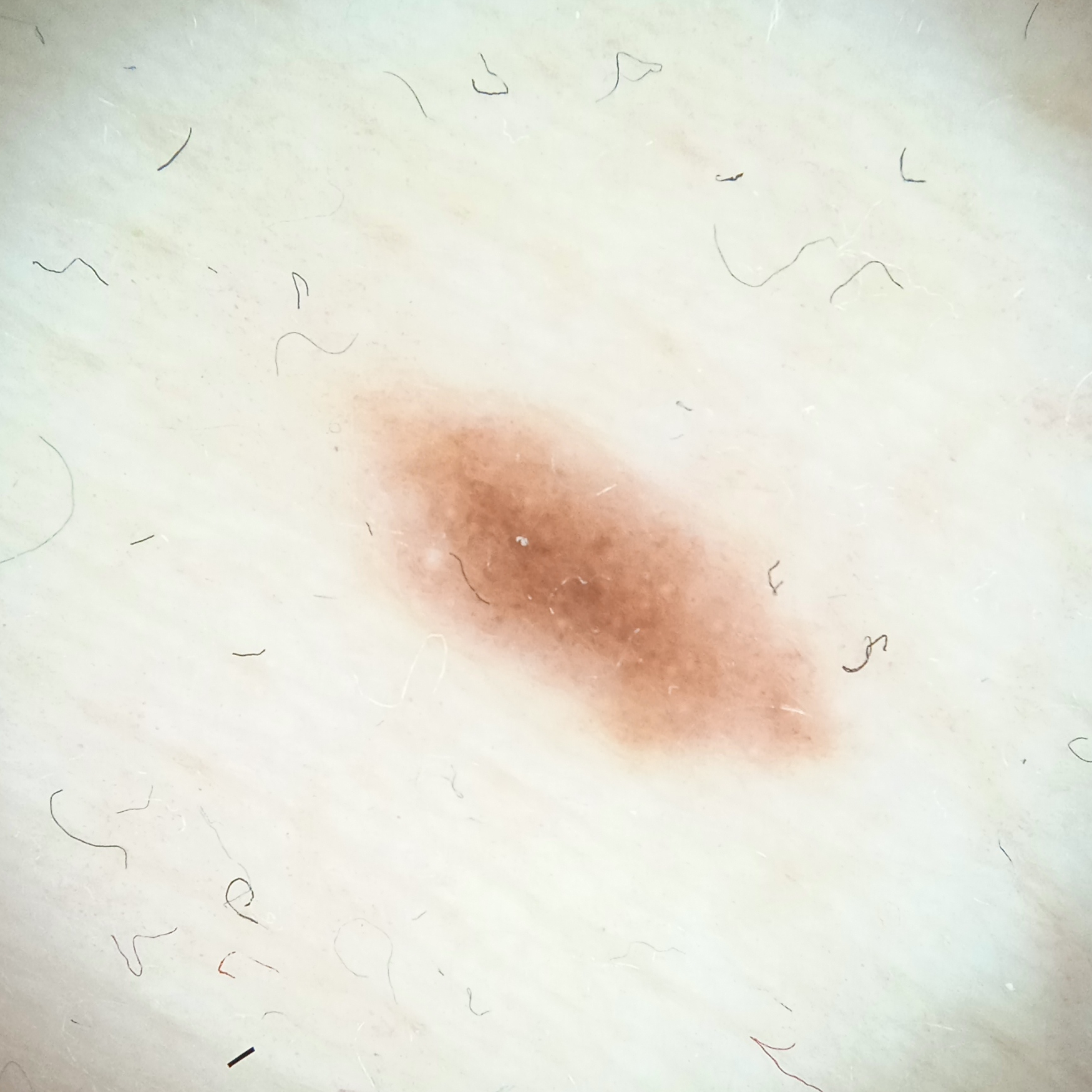A skin lesion imaged with a dermatoscope.
Imaged for a research study, with no referral diagnosis recorded.
A female patient 35 years of age.
The lesion is on the torso.
The lesion measures approximately 6.3 mm.
The consensus diagnosis for this lesion was a melanocytic nevus.